A dermoscopy image of a single skin lesion: 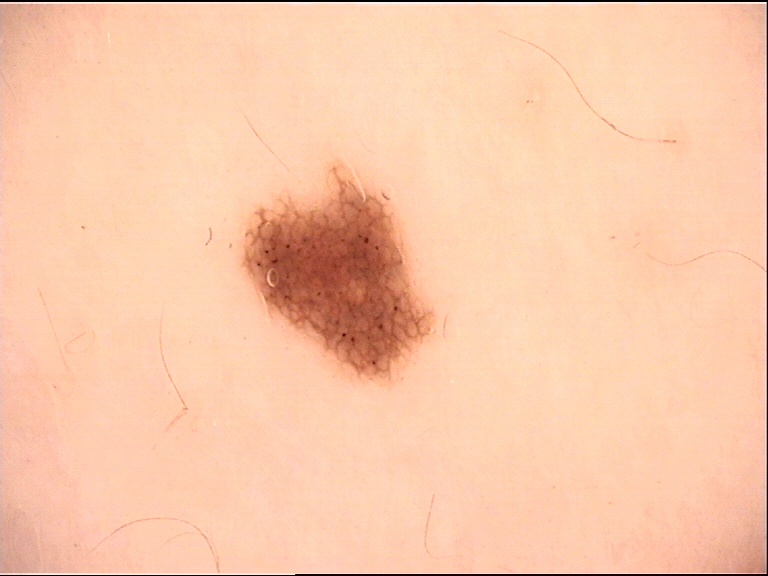Labeled as a dysplastic junctional nevus.